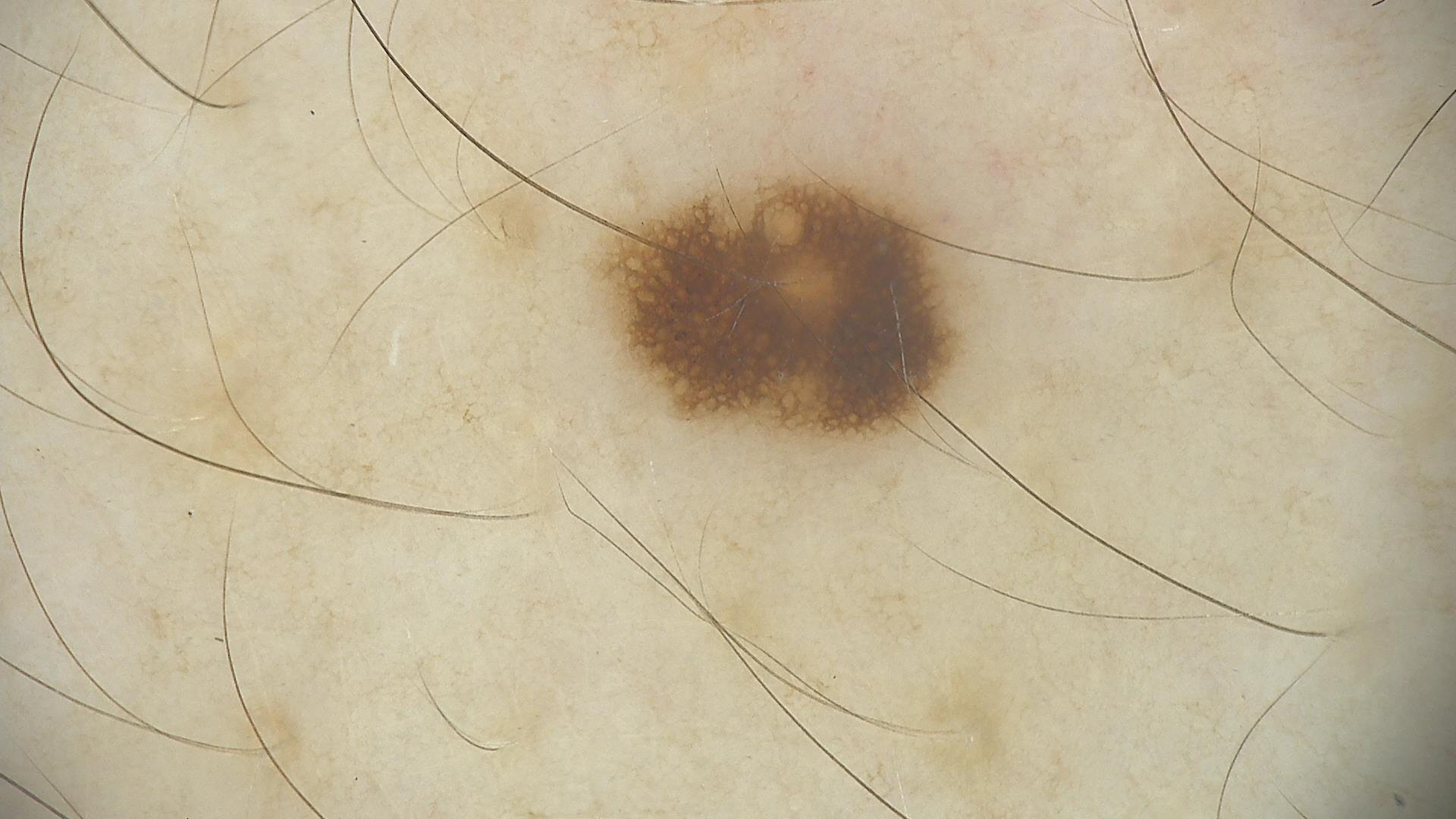modality — dermoscopy | class — dysplastic junctional nevus (expert consensus).